No associated systemic symptoms reported · reported lesion symptoms include itching · the patient reports the lesion is fluid-filled, rough or flaky and raised or bumpy · reported duration is one to three months · the contributor is female · the photograph is a close-up of the affected area: 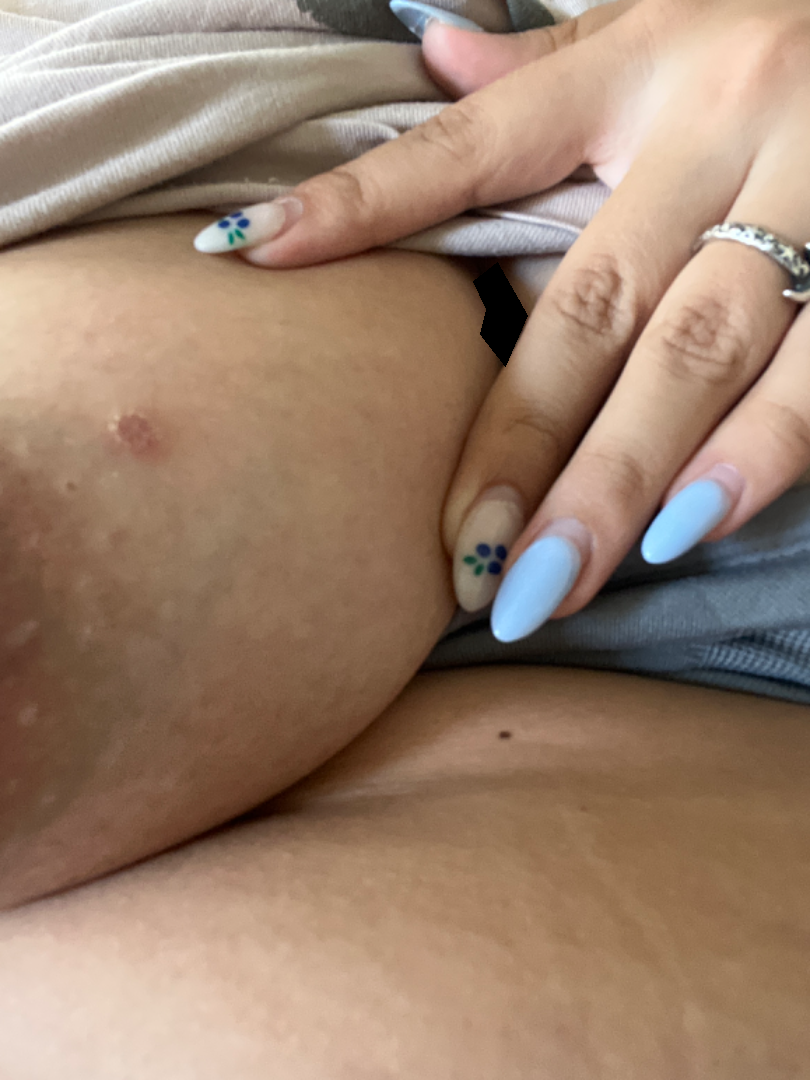The differential includes Eczema, Abscess and Impetigo, with no clear leading consideration.